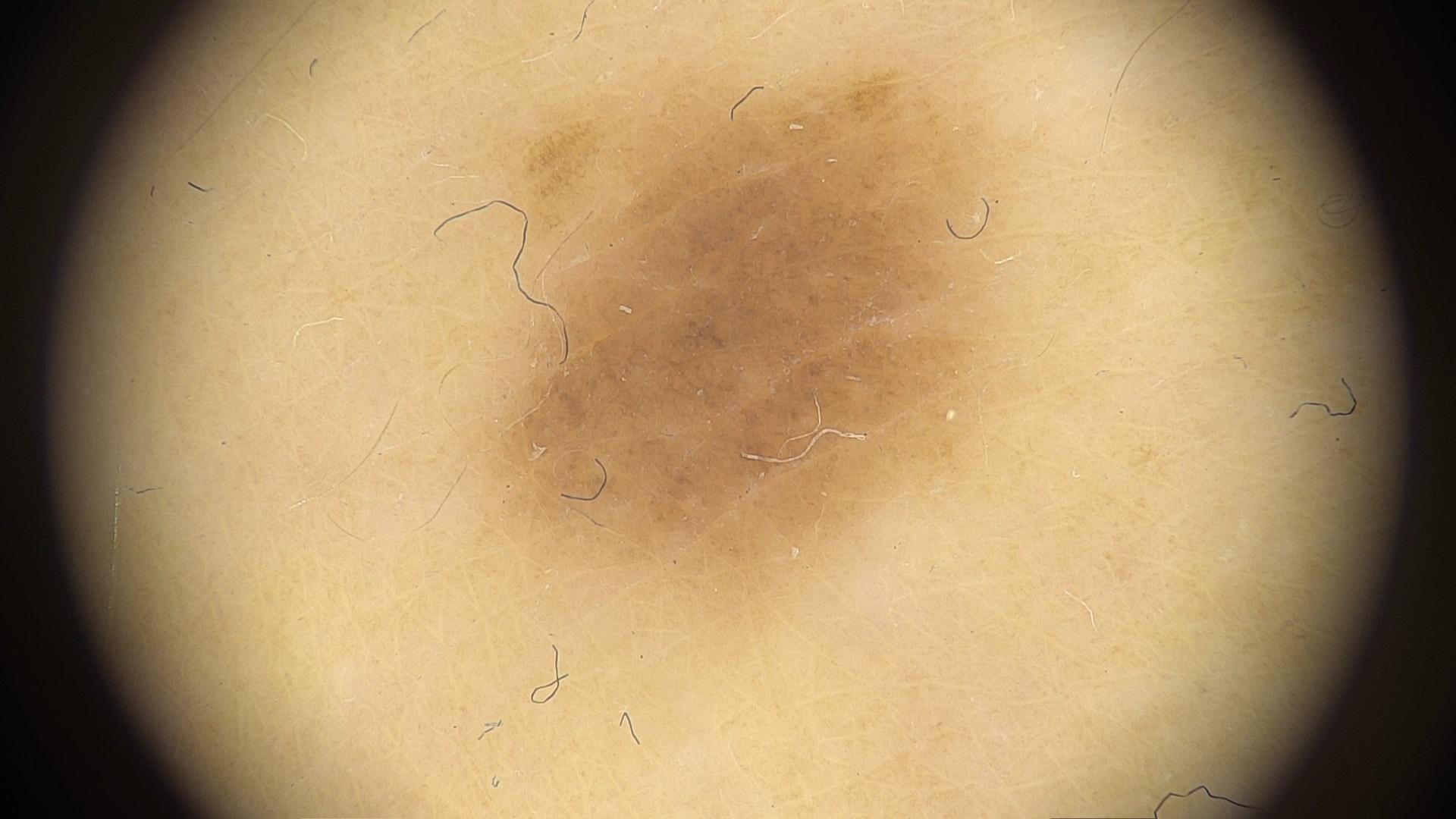Q: What is this lesion?
A: Nevus